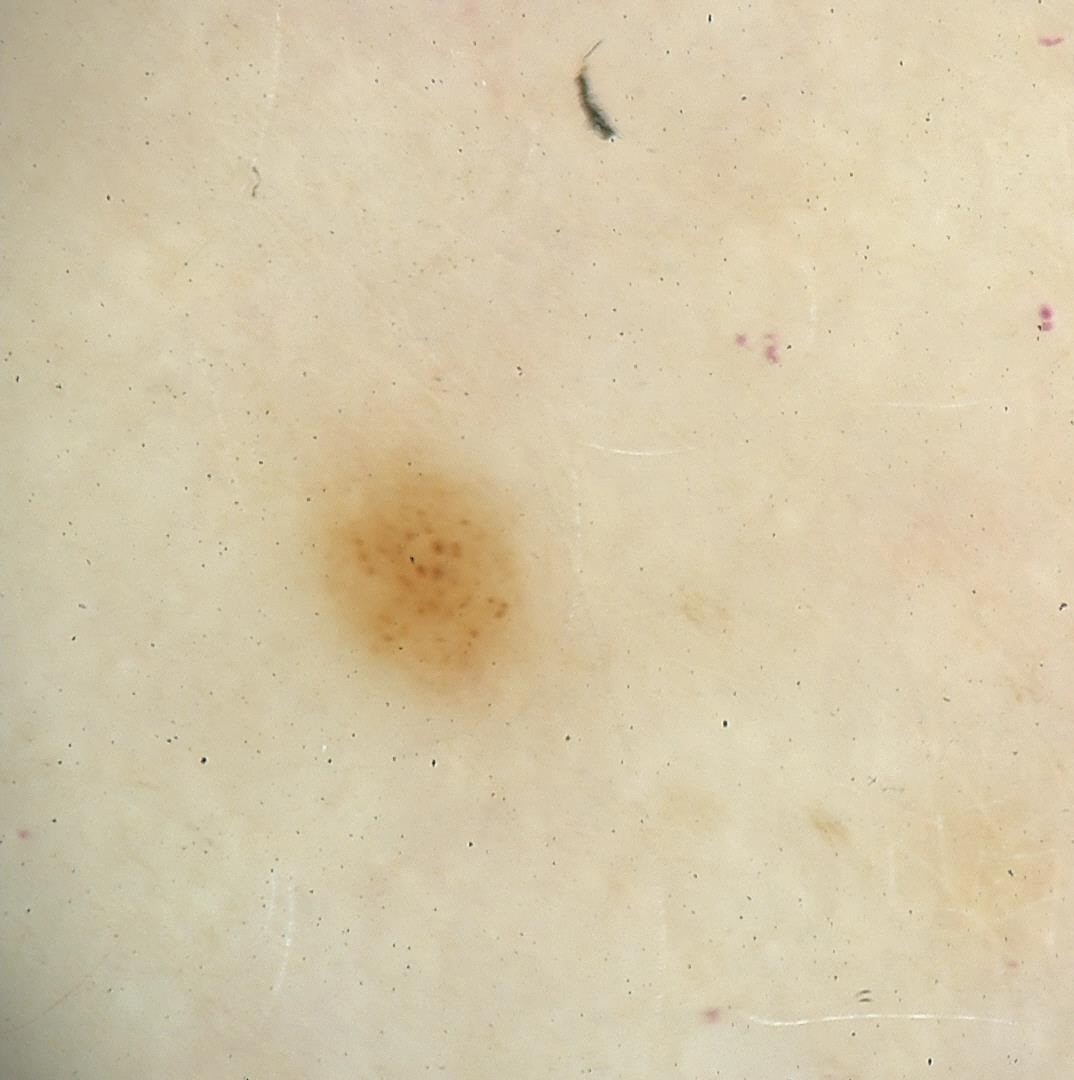diagnosis=junctional nevus (expert consensus)